The affected area is the arm · the condition has been present for one to three months · no associated systemic symptoms reported · self-categorized by the patient as a rash · symptoms reported: enlargement, itching and bothersome appearance · the lesion is described as rough or flaky · close-up view:
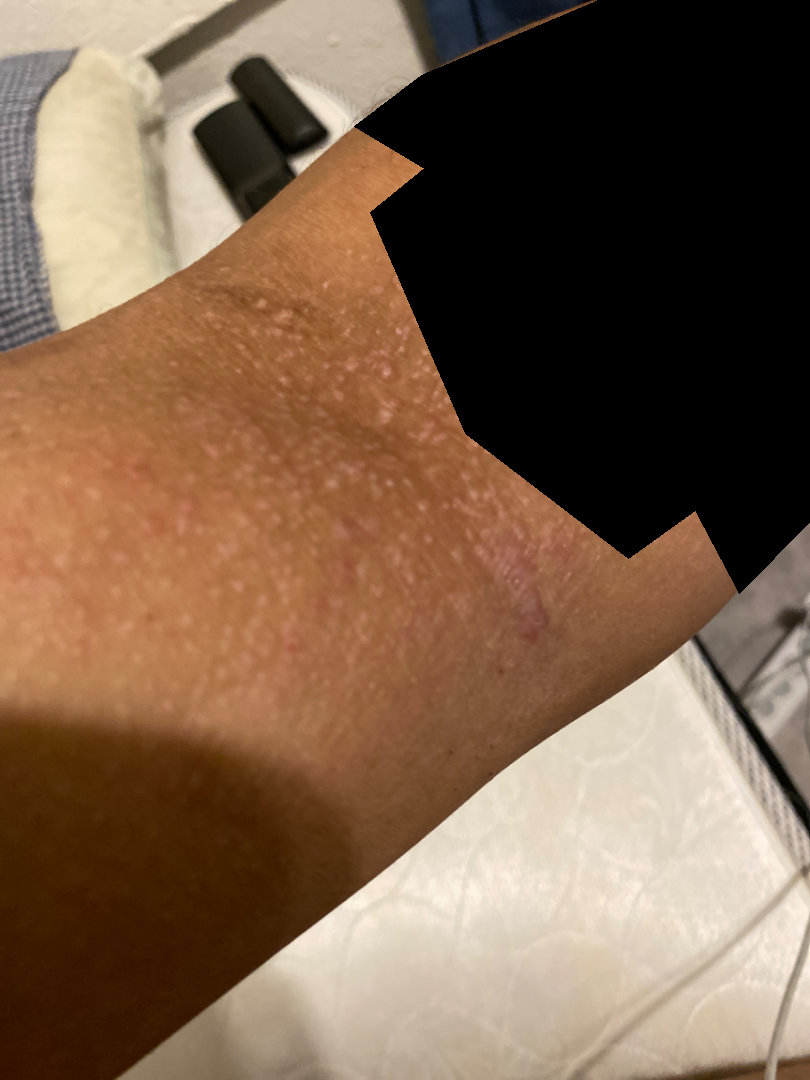A single dermatologist reviewed the case: consistent with Eczema.